A dermoscopy image of a single skin lesion.
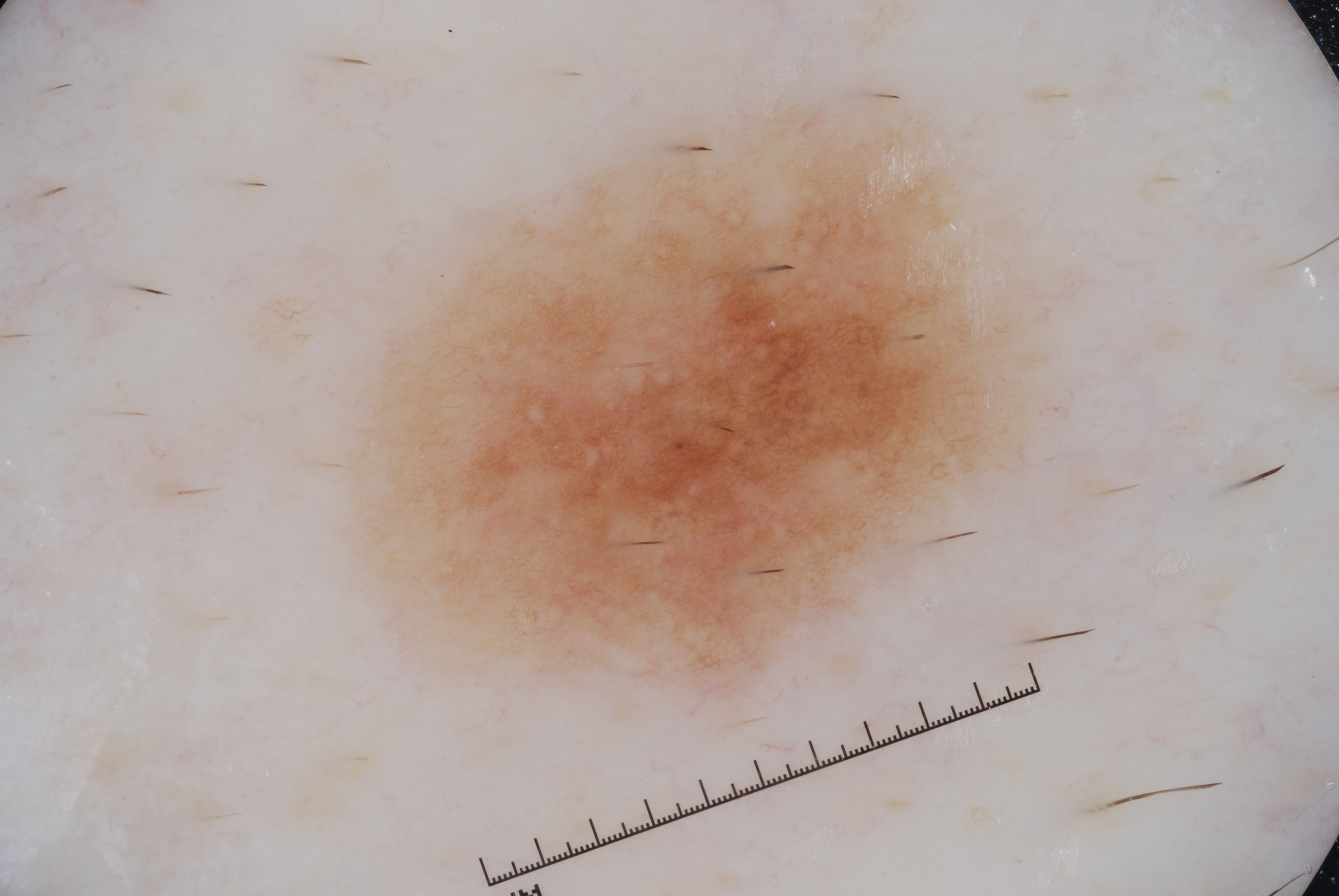The lesion is located at (366, 105, 1025, 693).
Confirmed on histopathology as a melanoma.